The patient says their skin reddens with sun exposure. Collected as part of a research study, without a referral diagnosis.
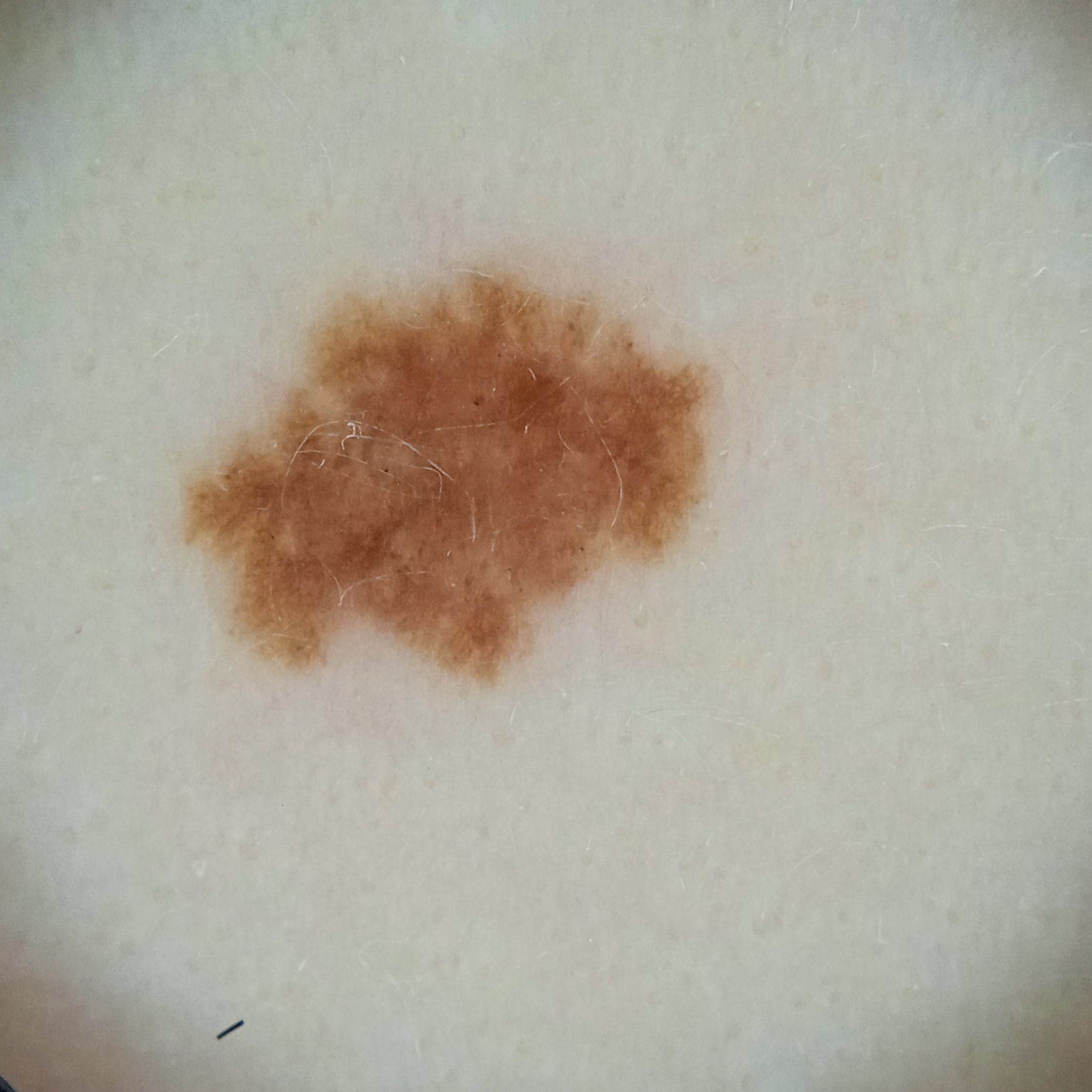The lesion involves an arm. Measuring roughly 6.4 mm. The four-dermatologist consensus diagnosis was an atypical (dysplastic) nevus; agreement among the reviewers was unanimous; the reviewers were fairly confident; the differential also included a melanoma.